Acquired for a research image collection, with no referral diagnosis · a dermoscopy image of a skin lesion · a male patient aged 83 — 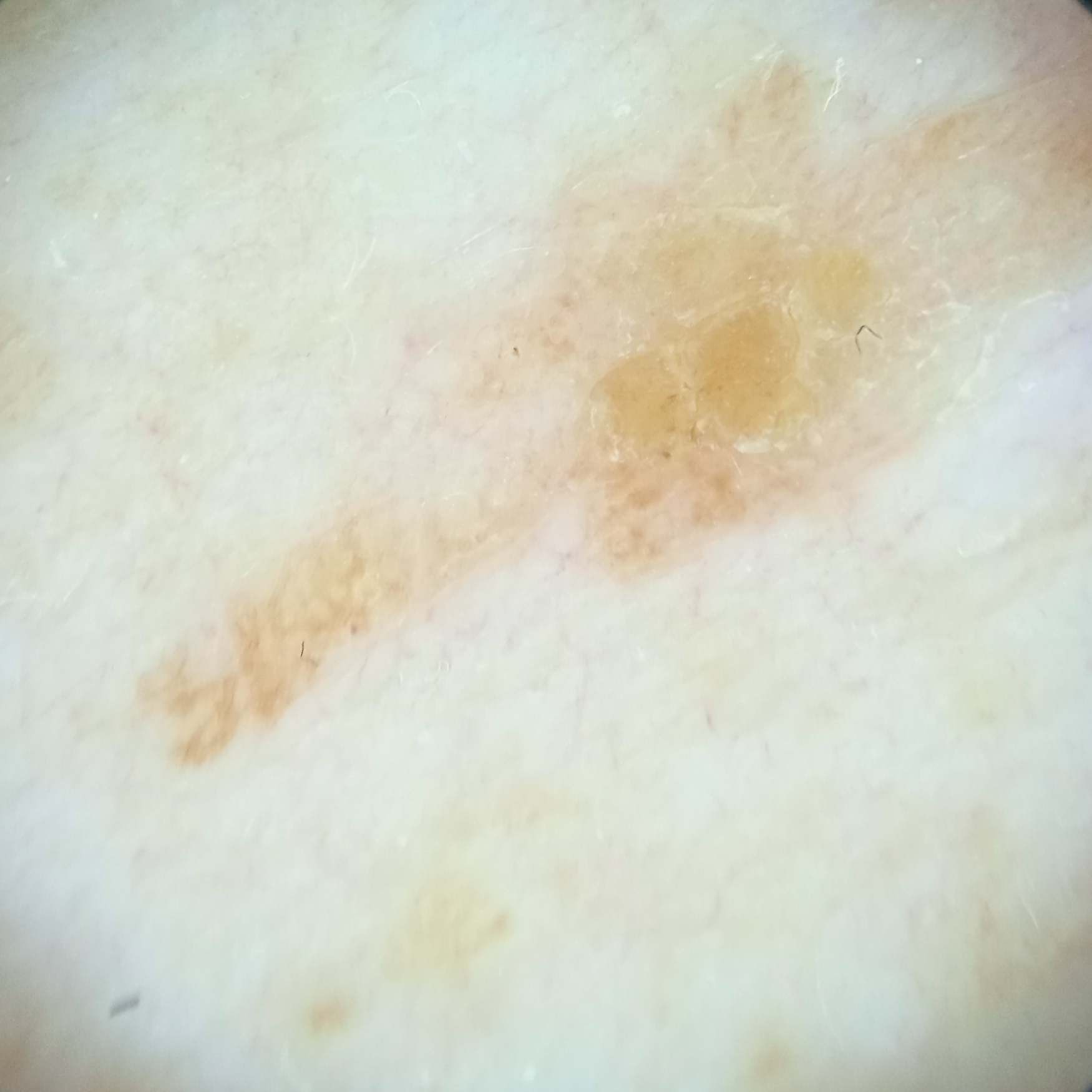Clinical context:
The lesion is located on the back. The lesion is about 16.4 mm across.
Impression:
The lesion was assessed as a seborrheic keratosis.